The photograph was taken at a distance; the front of the torso, back of the hand, back of the torso and arm are involved; female contributor, age 50–59 — 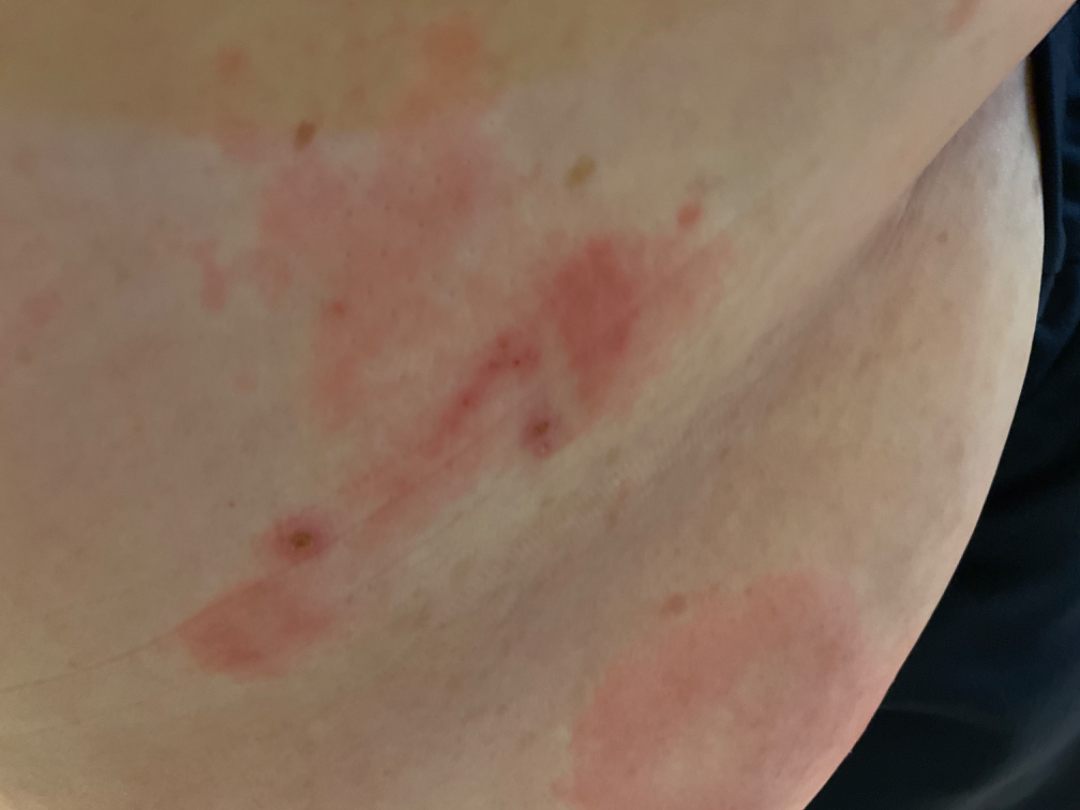Q: Could the case be diagnosed?
A: not assessable
Q: Reported symptoms?
A: itching, enlargement and bothersome appearance
Q: Patient's own categorization?
A: a rash
Q: How does the lesion feel?
A: raised or bumpy
Q: When did this start?
A: one to four weeks